A close-up photograph, located on the arm and leg.
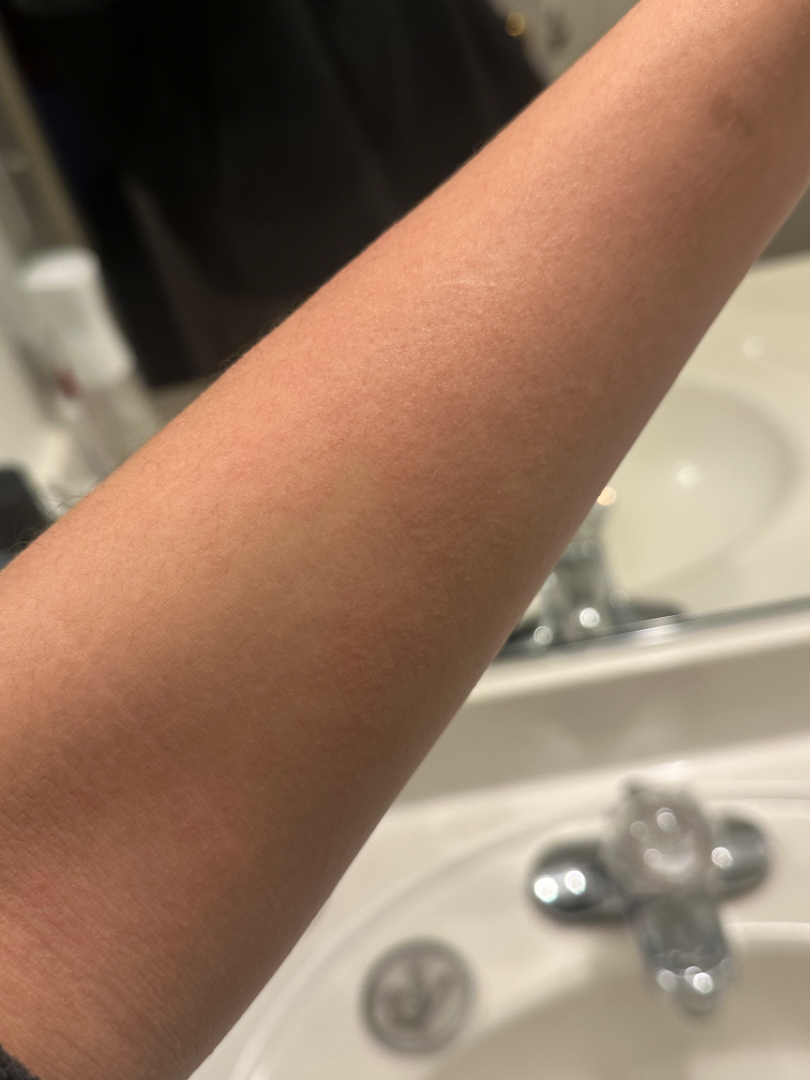On photographic review: Drug Rash, Viral Exanthem and Hypersensitivity were each considered, in no particular order.